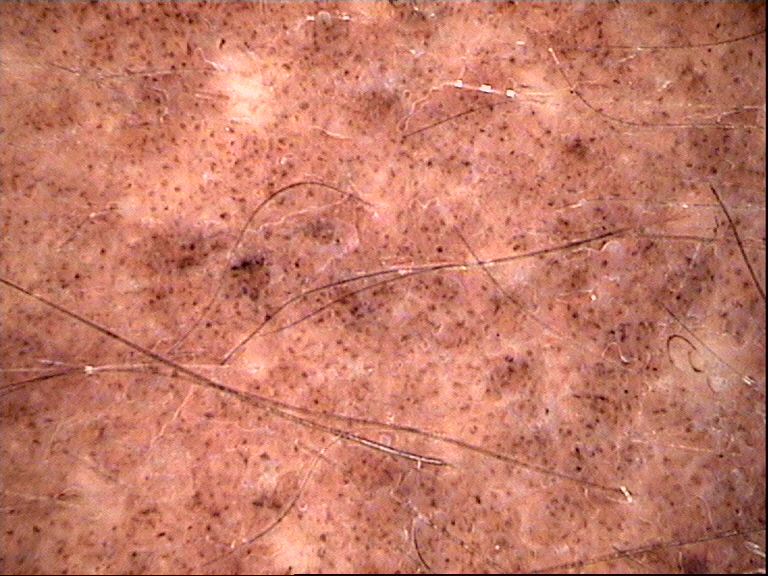A skin lesion imaged with a dermatoscope. This is a banal lesion. The diagnosis was a congenital compound nevus.